A male subject roughly 65 years of age. A dermatoscopic image of a skin lesion.
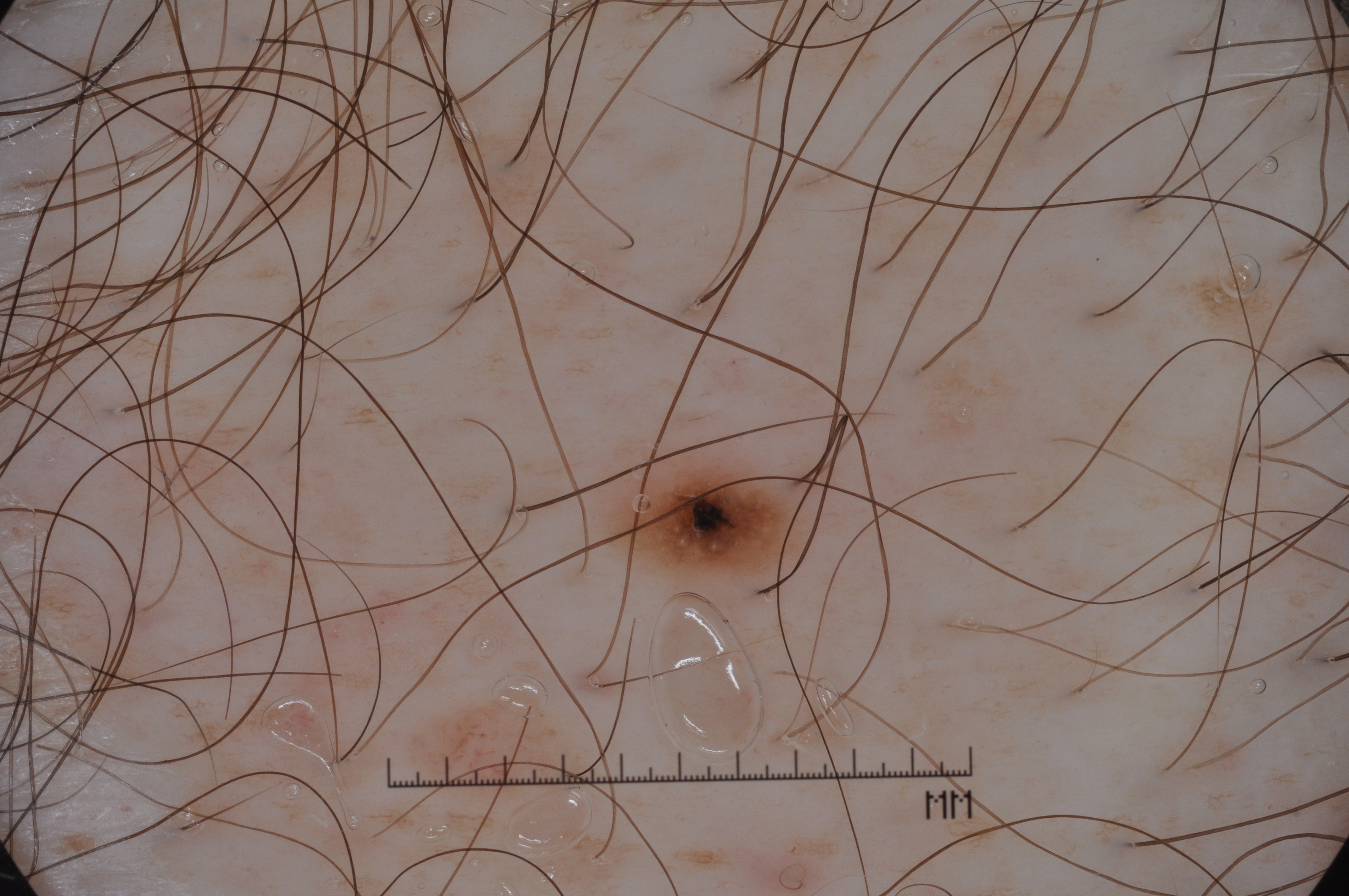Image and clinical context:
The lesion spans x1=596 y1=419 x2=819 y2=598. Dermoscopically, the lesion shows milia-like cysts and pigment network; no negative network or streaks. The lesion occupies roughly 2% of the field.
Conclusion:
The diagnostic assessment was a melanocytic nevus.